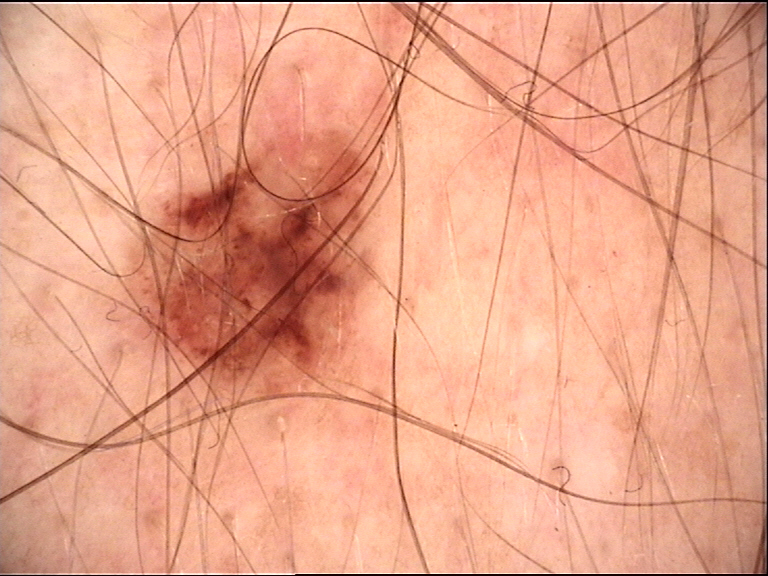A dermoscopic photograph of a skin lesion. Consistent with a banal lesion — a junctional nevus.